An image taken at a distance · the affected area is the back of the hand — 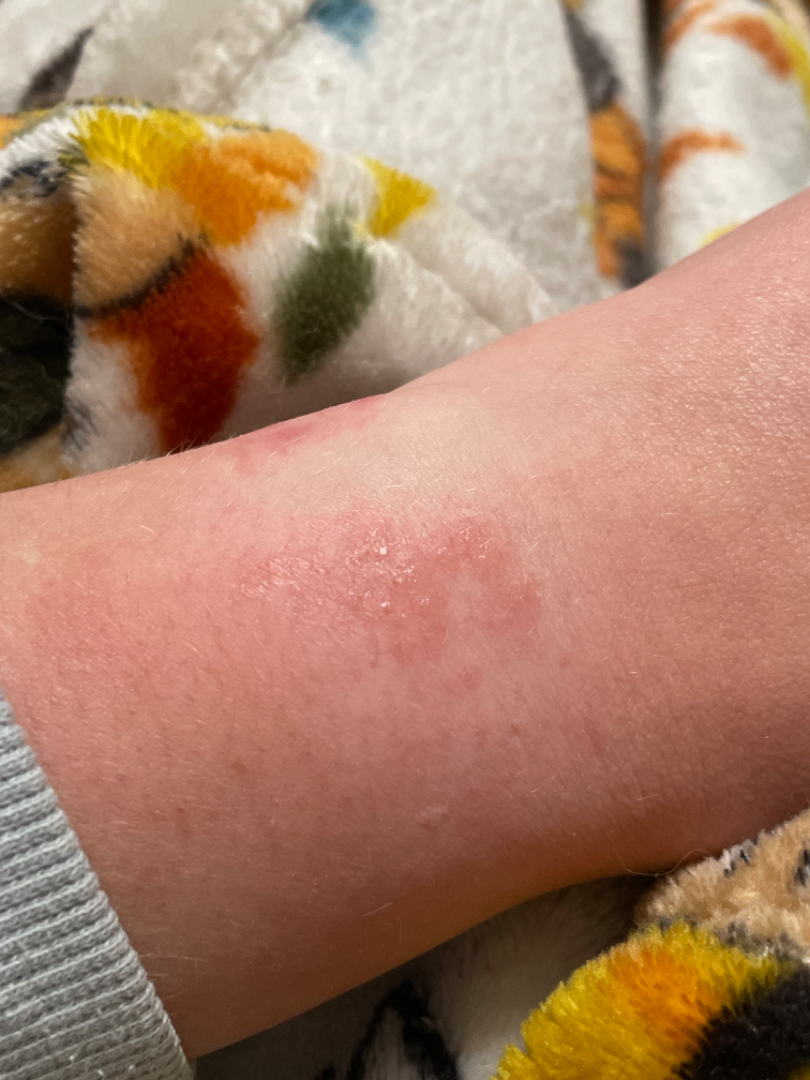The patient notes the lesion is raised or bumpy. The patient considered this a rash. No constitutional symptoms were reported. Present for less than one week. Most consistent with Allergic Contact Dermatitis.